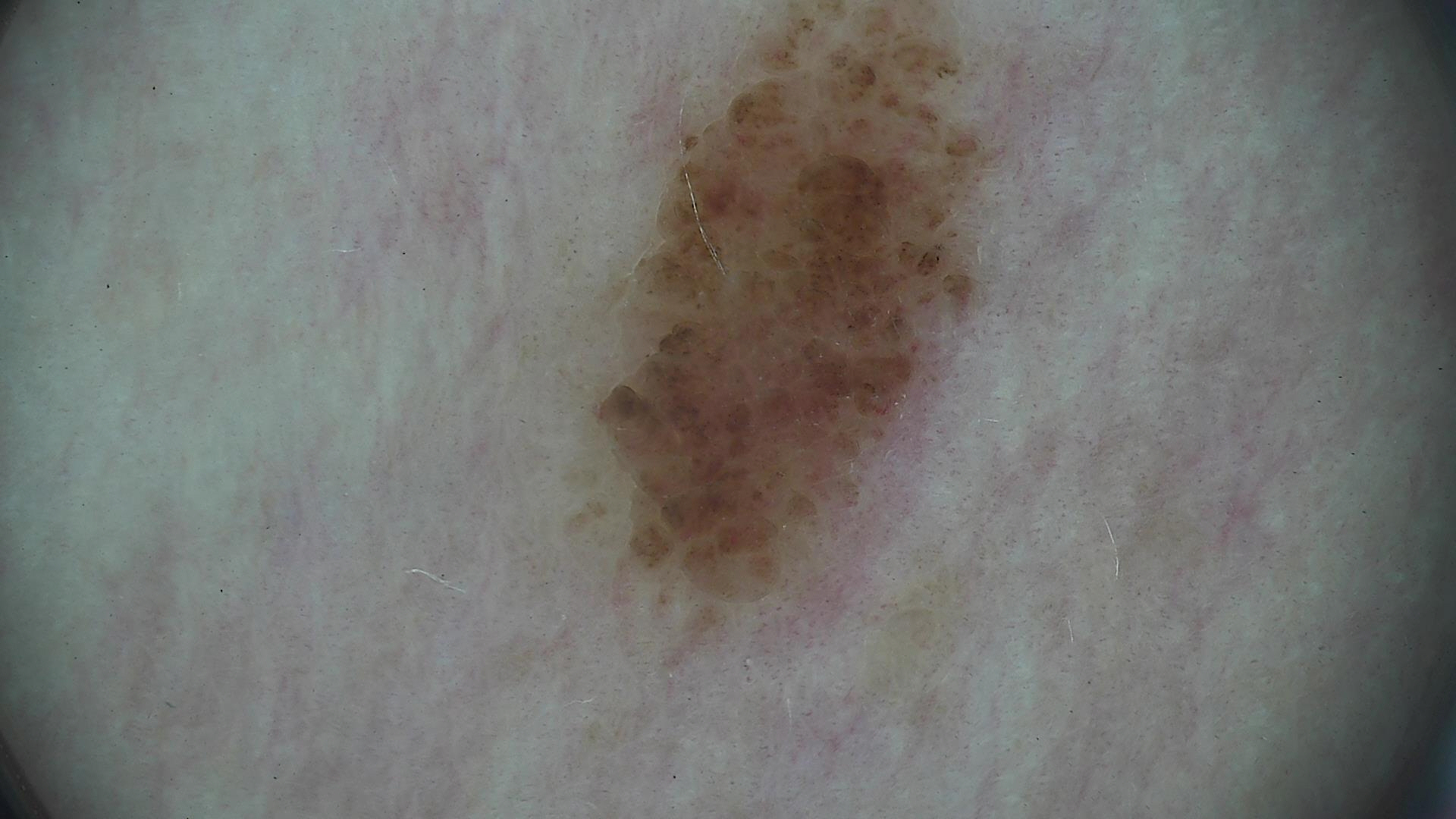A dermatoscopic image of a skin lesion. Consistent with a banal lesion — a compound nevus.